A male subject approximately 40 years of age, a skin lesion imaged with a dermatoscope: 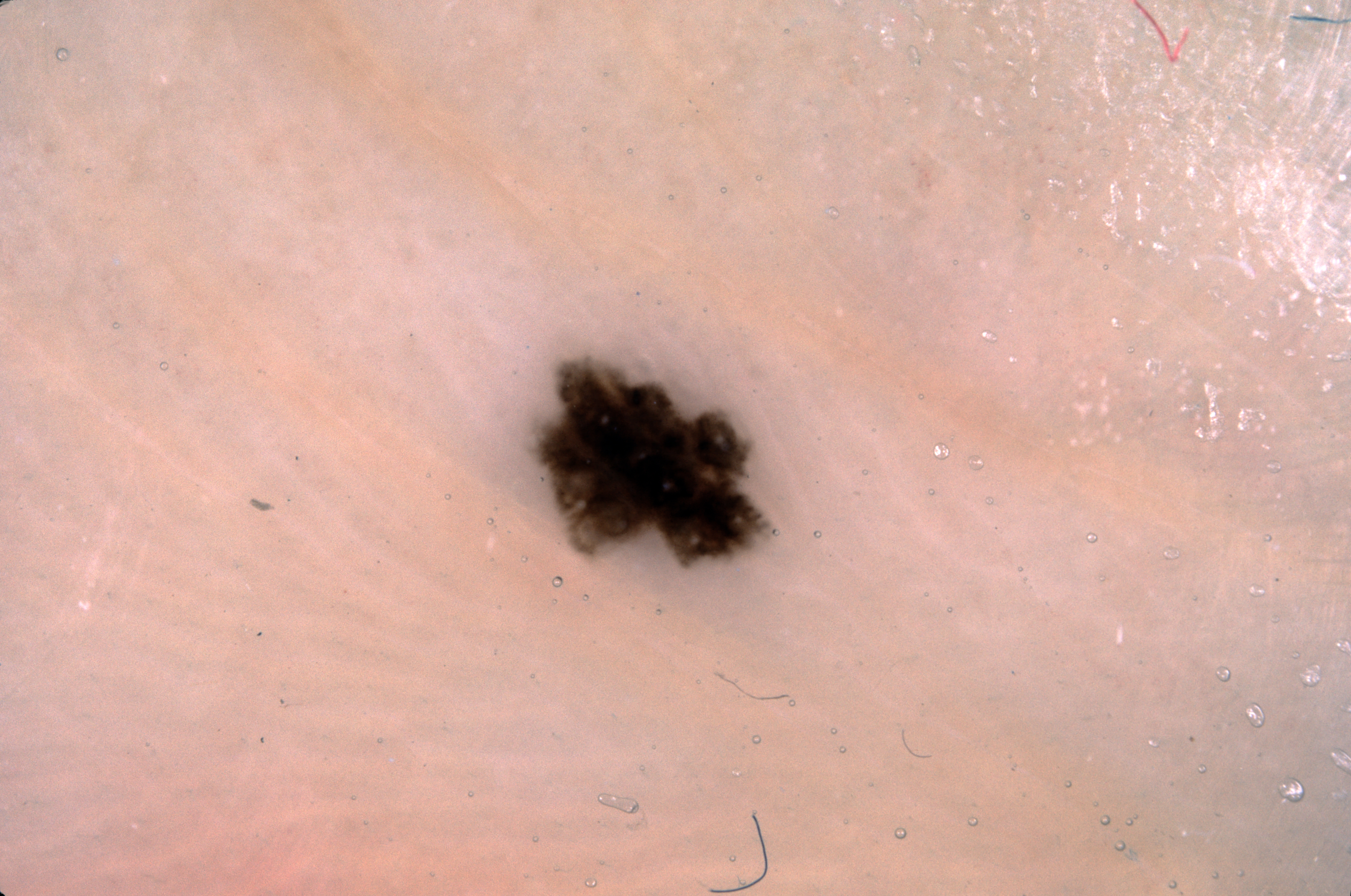In (x1, y1, x2, y2) order, the lesion occupies the region [526, 354, 776, 571]. A small lesion within a wider field of skin. The dermoscopic pattern shows no milia-like cysts, streaks, negative network, or pigment network. Diagnosed as a melanocytic nevus.